The lesion is associated with bothersome appearance, the condition has been present for one to four weeks, this is a close-up image, located on the front of the torso, texture is reported as flat — 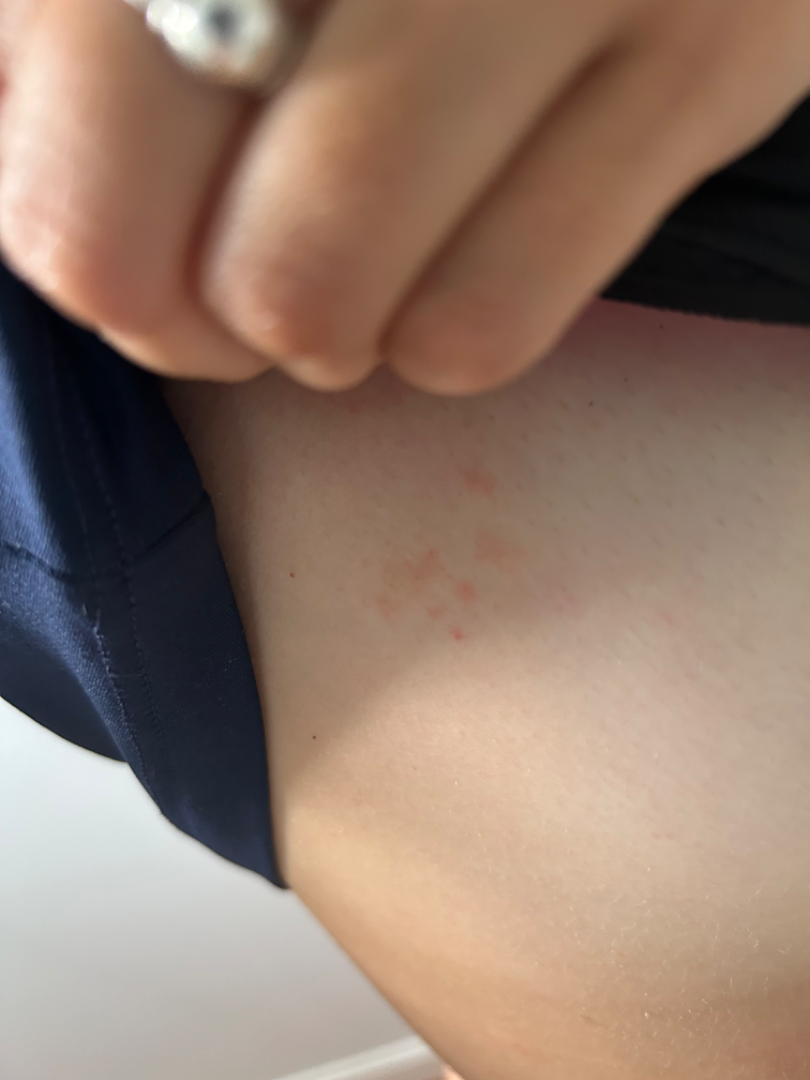assessment: indeterminate from the photograph.